A dermoscopic close-up of a skin lesion, the subject is a female in their 80s.
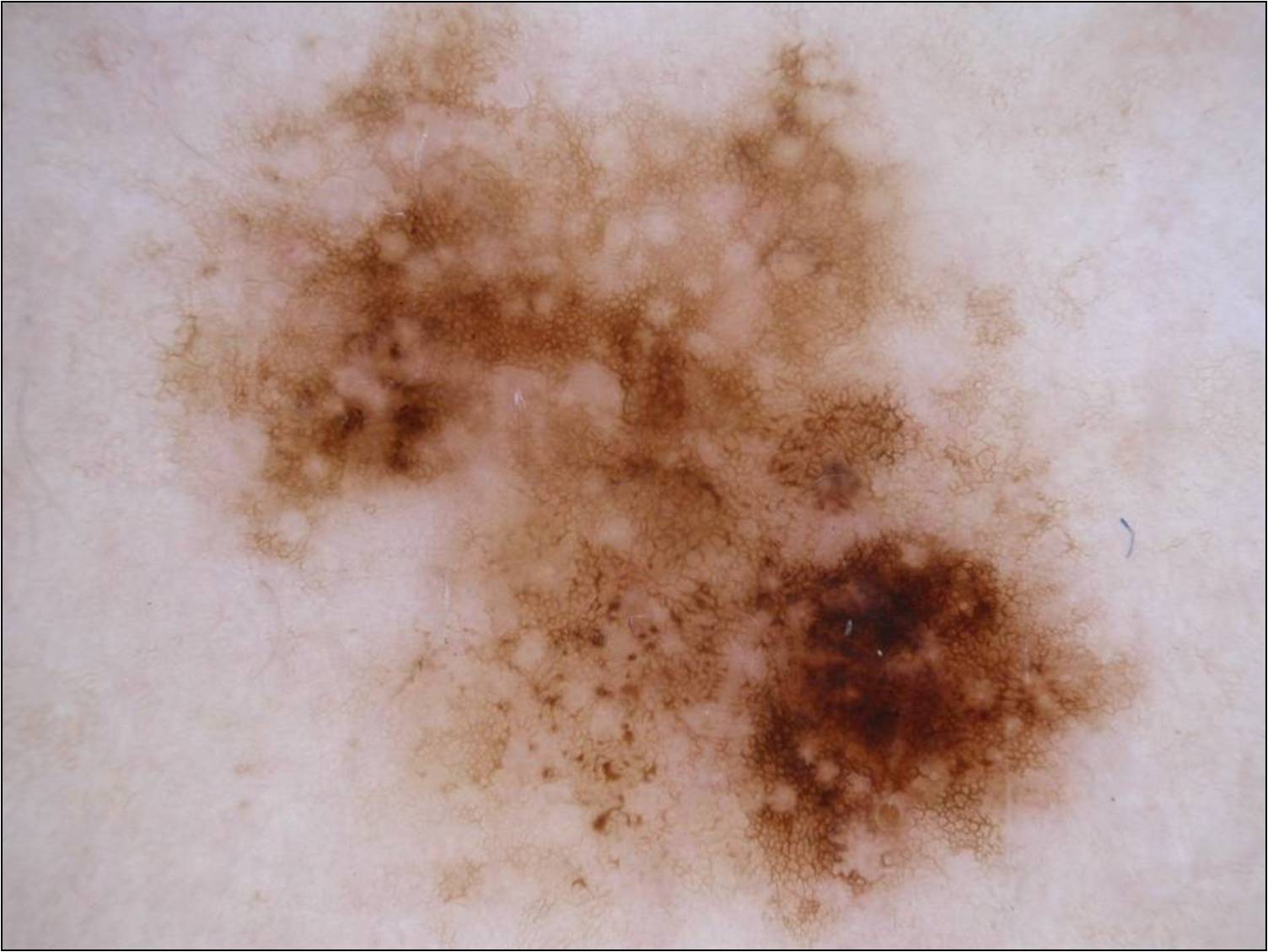dermoscopic findings: pigment network and globules | lesion bbox: bbox=[94, 3, 1195, 902] | lesion size: ~65% of the field | diagnosis: a melanoma.